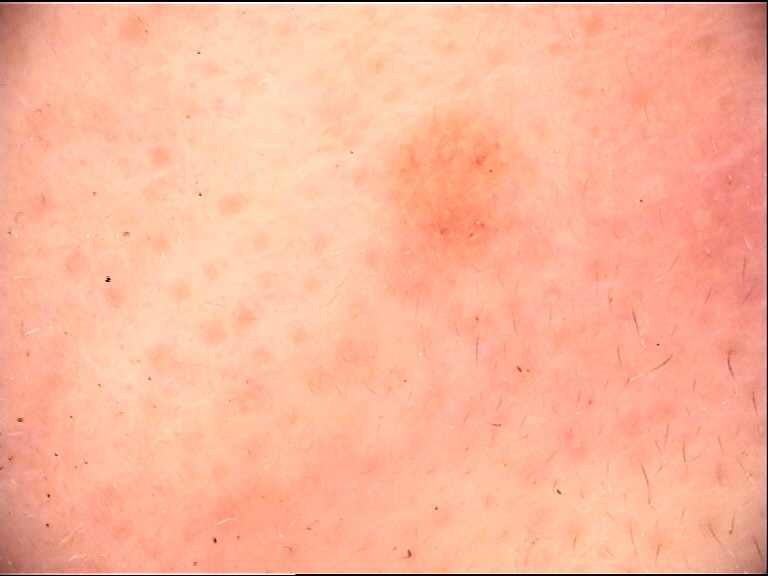Findings:
A dermoscopic close-up of a skin lesion. The architecture is that of a banal lesion.
Conclusion:
The diagnosis was a dermal nevus.